A dermoscopic close-up of a skin lesion.
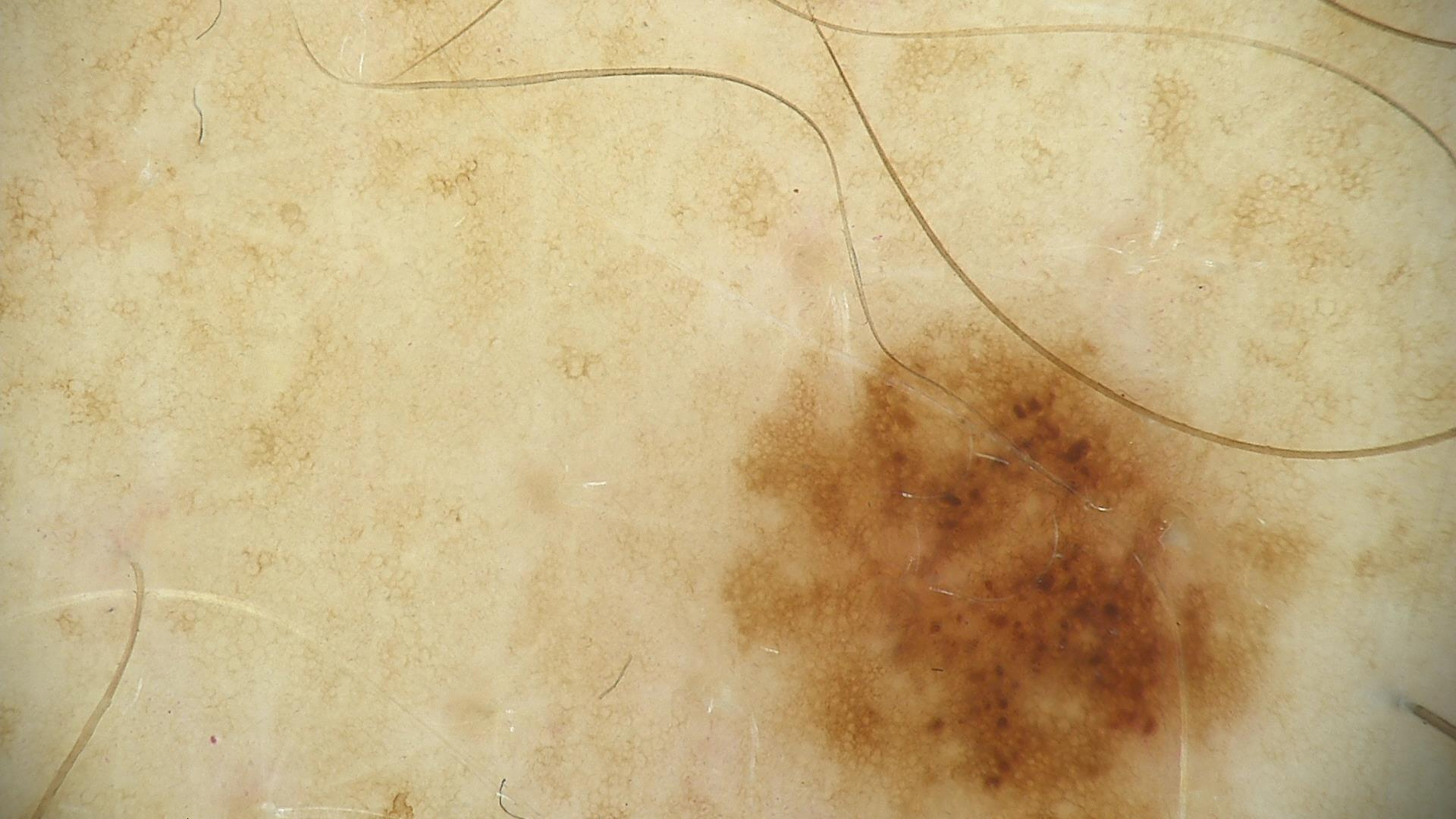Impression:
Consistent with a dysplastic junctional nevus.